A close-up photograph. The affected area is the back of the hand and palm: 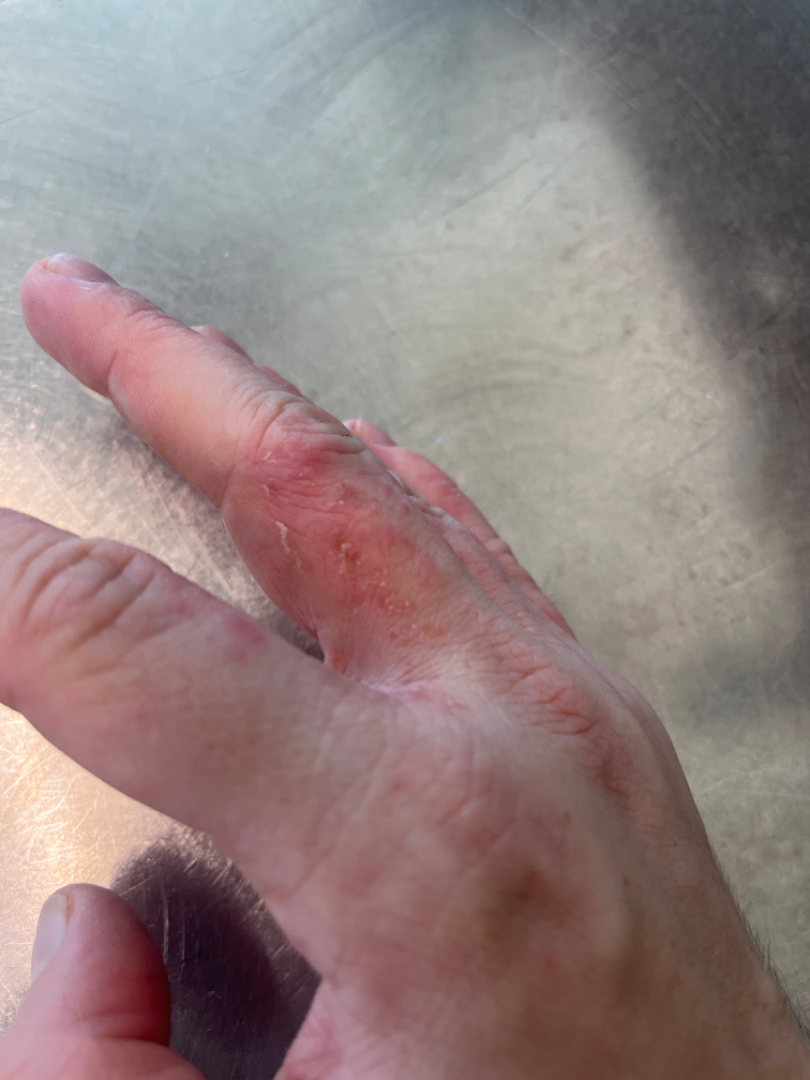Eczema (weight 0.46); Irritant Contact Dermatitis (weight 0.31); Scabies (weight 0.23).